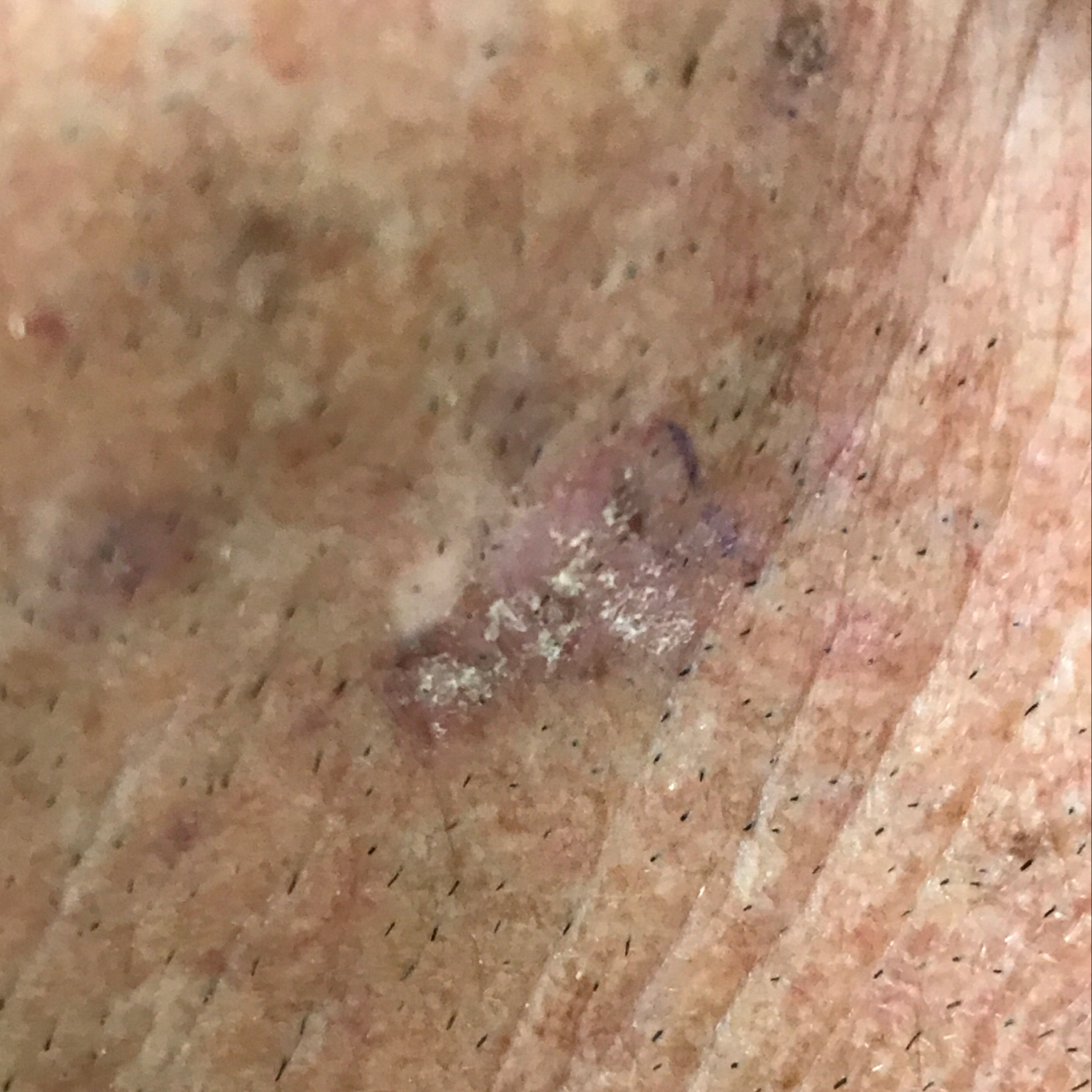diagnostic label=actinic keratosis (biopsy-proven)